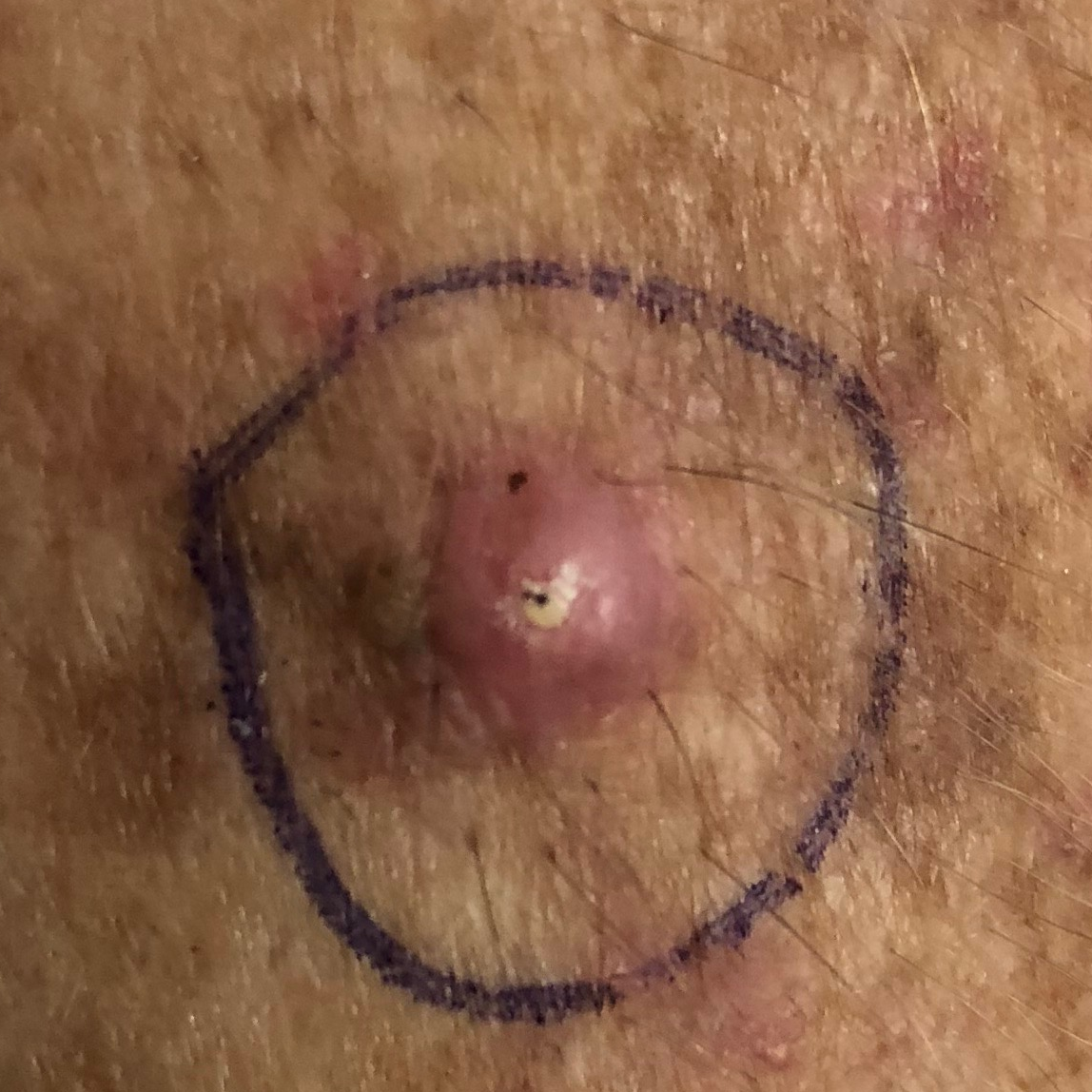Q: What is this lesion?
A: squamous cell carcinoma (biopsy-proven)